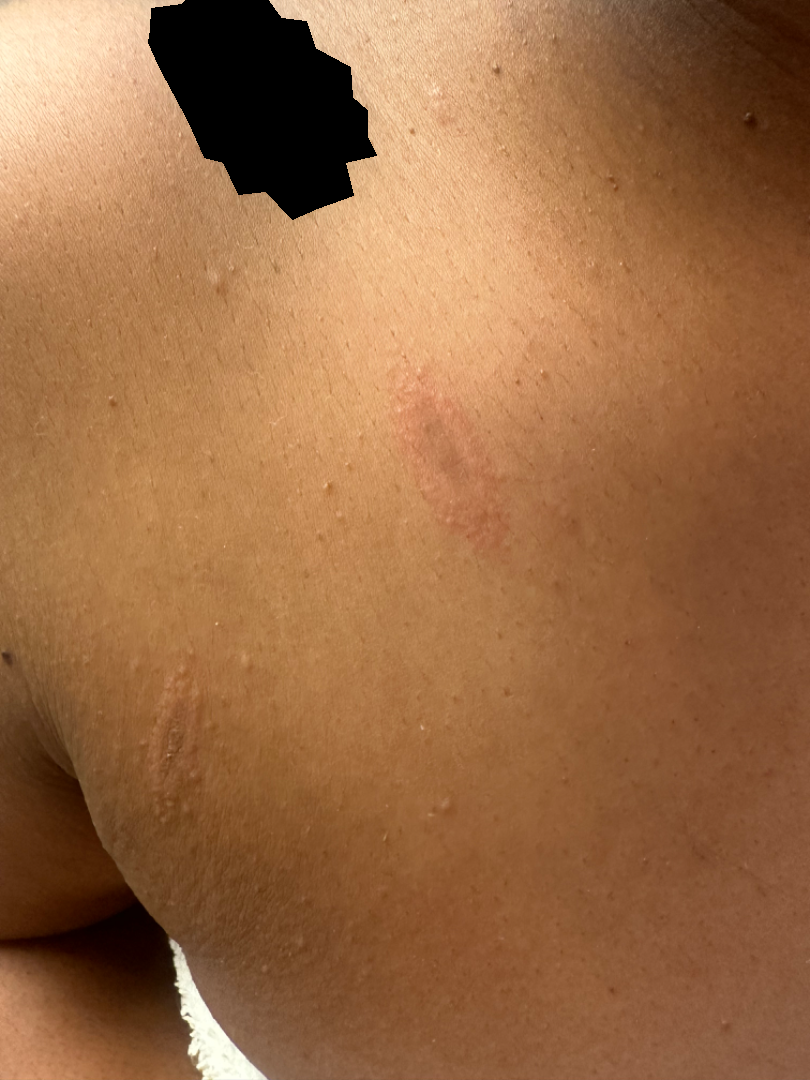History:
The contributor notes the condition has been present for about one day. The photograph was taken at an angle. Texture is reported as rough or flaky. The patient considered this a rash. The contributor notes bothersome appearance and darkening.
Impression:
On teledermatology review, Erythema multiforme (100%).